A dermoscopic close-up of a skin lesion.
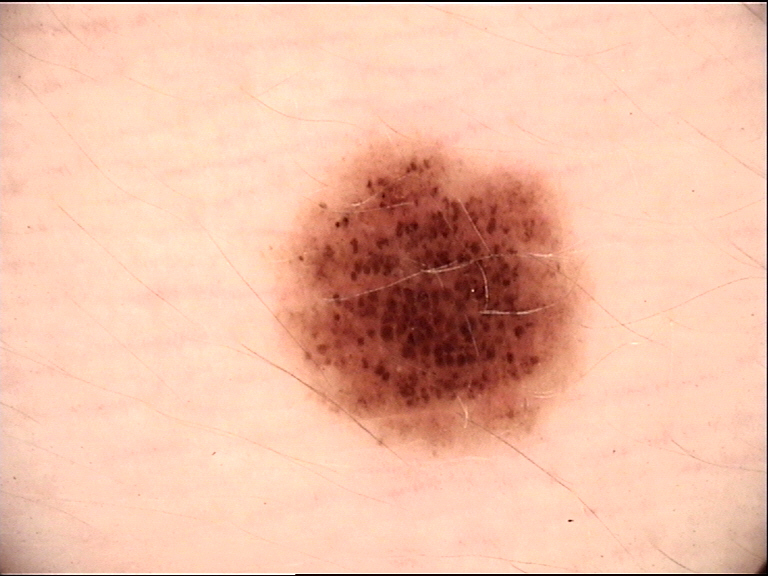The diagnosis was a dysplastic junctional nevus.